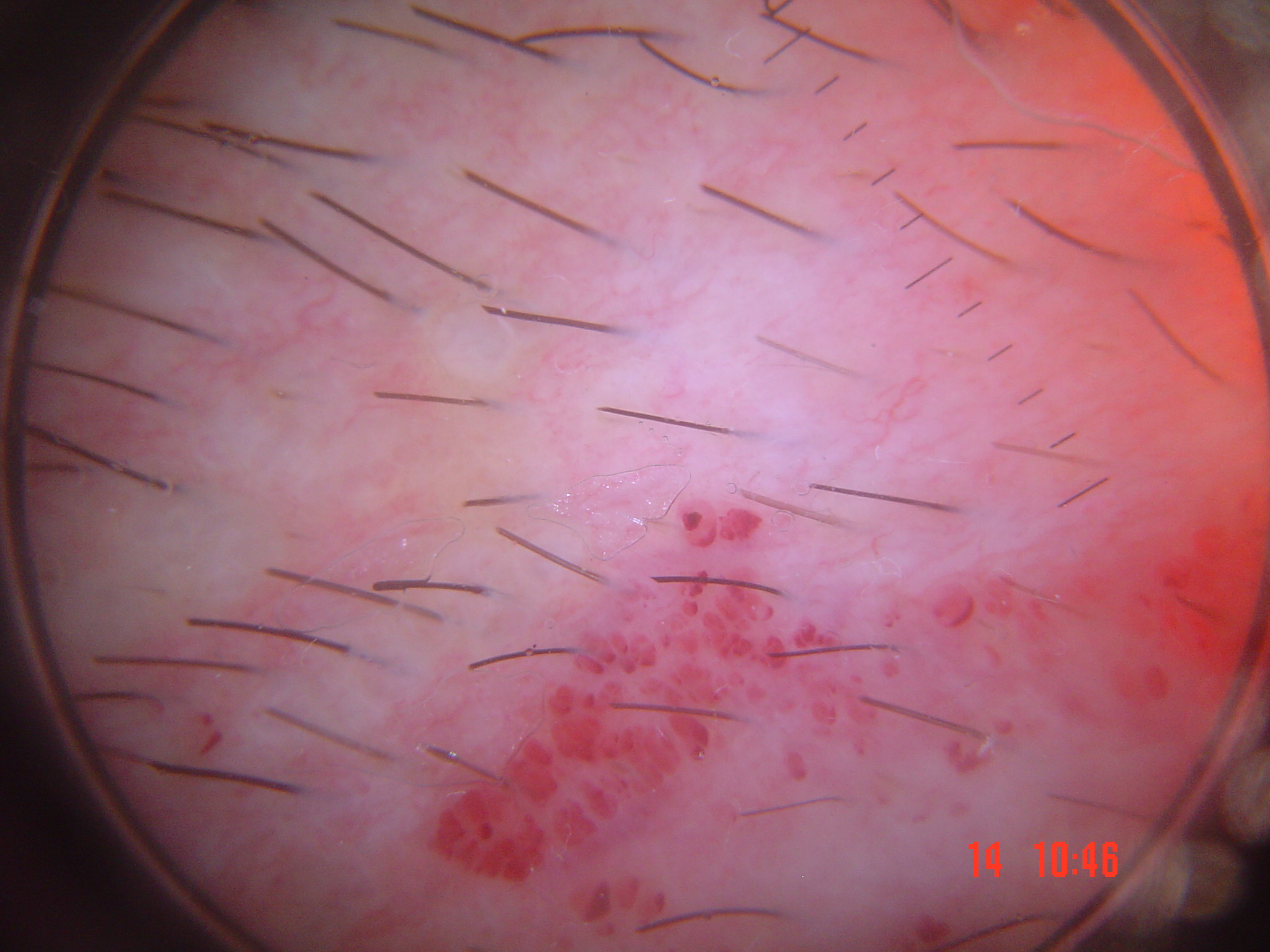imaging: dermoscopy
class: lymphangioma (expert consensus)